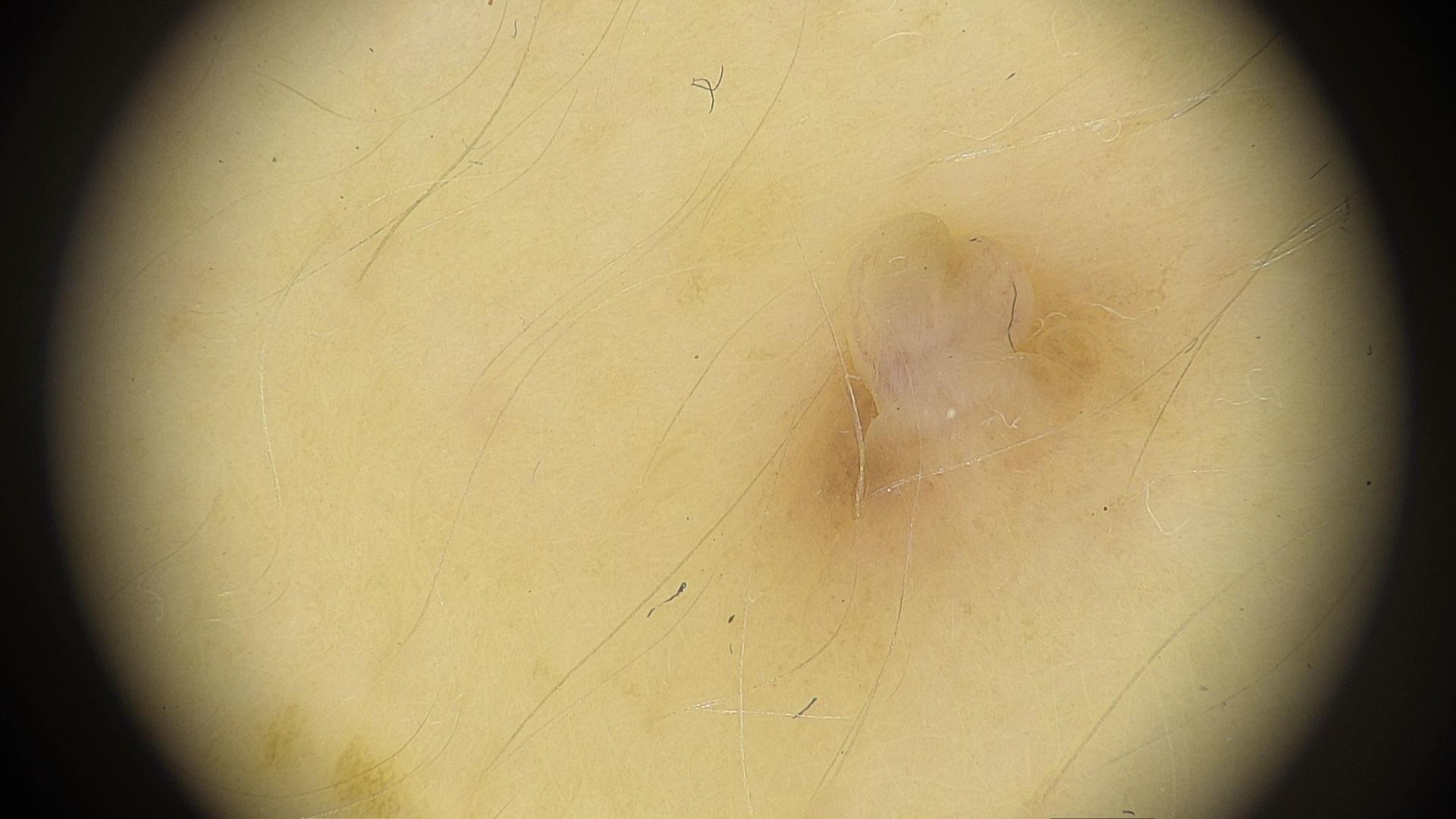Contact-polarized dermoscopy of a skin lesion.
A female patient aged 48-52.
Clinically diagnosed as a nevus.